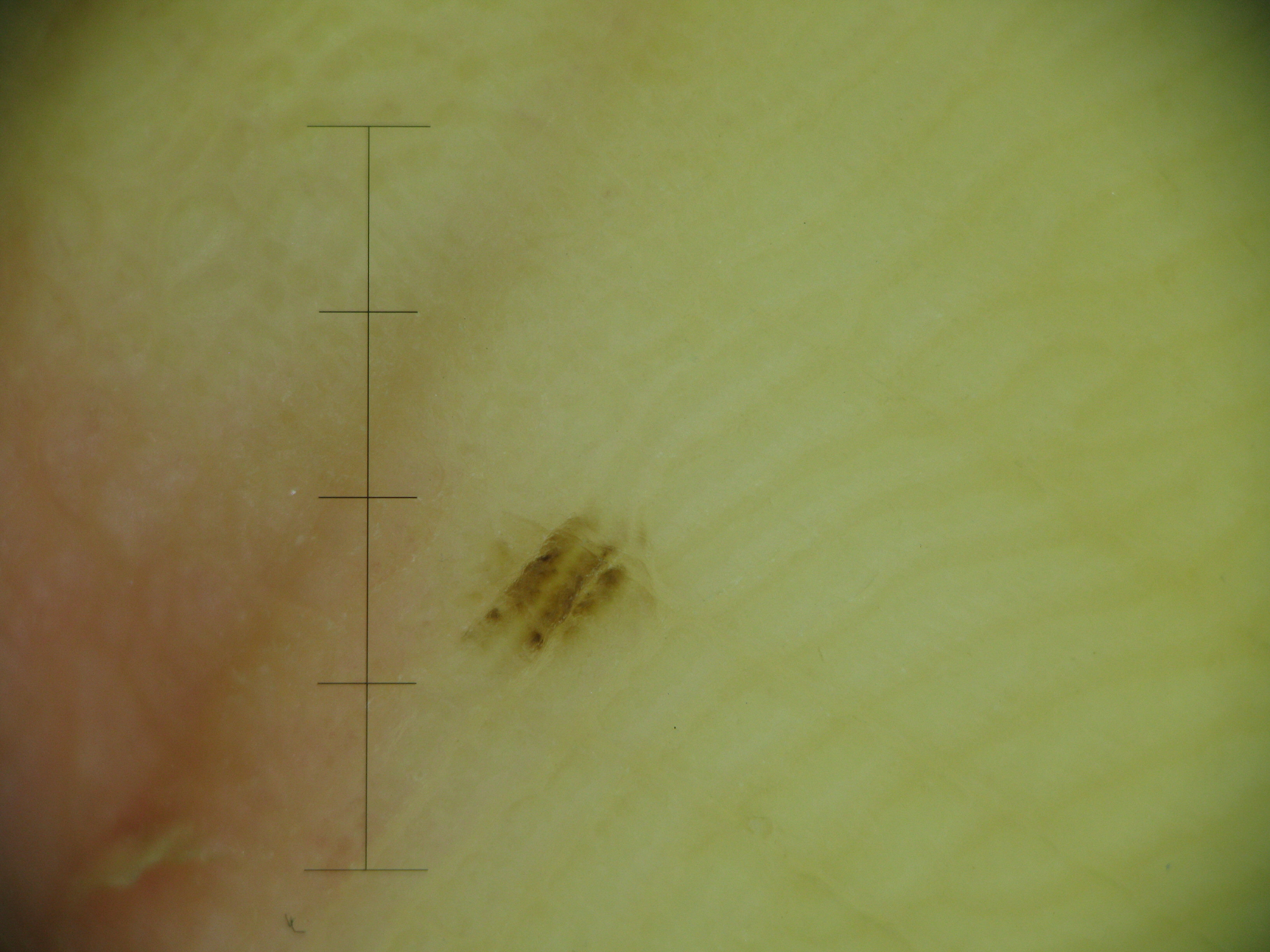  image: dermatoscopy
  lesion_type:
    main_class: banal
    pattern: junctional
  diagnosis:
    name: acral junctional nevus
    code: ajb
    malignancy: benign
    super_class: melanocytic
    confirmation: expert consensus